A dermoscopic close-up of a skin lesion.
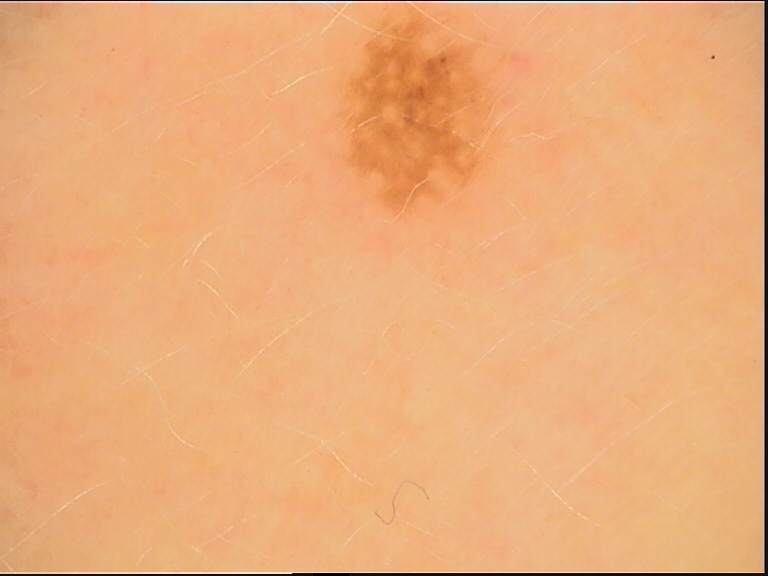Consistent with a keratinocytic lesion — a seborrheic keratosis.